A dermatoscopic image of a skin lesion.
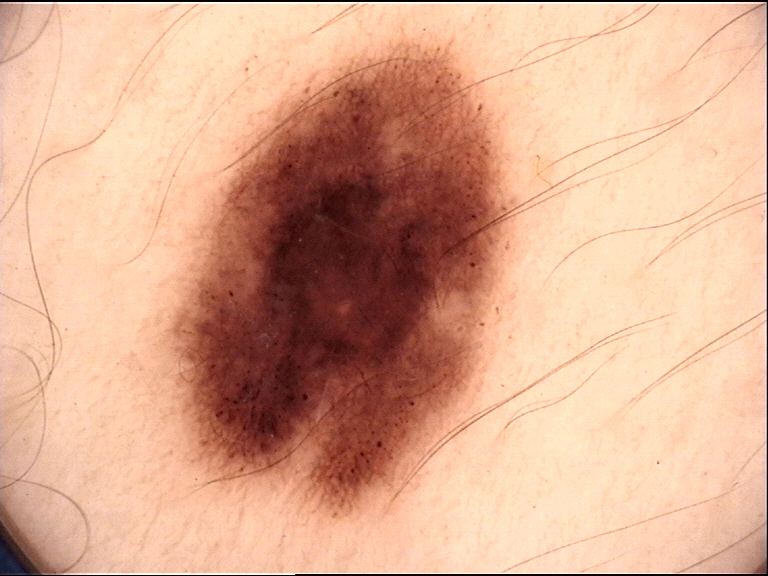Findings:
- class — dysplastic junctional nevus (expert consensus)